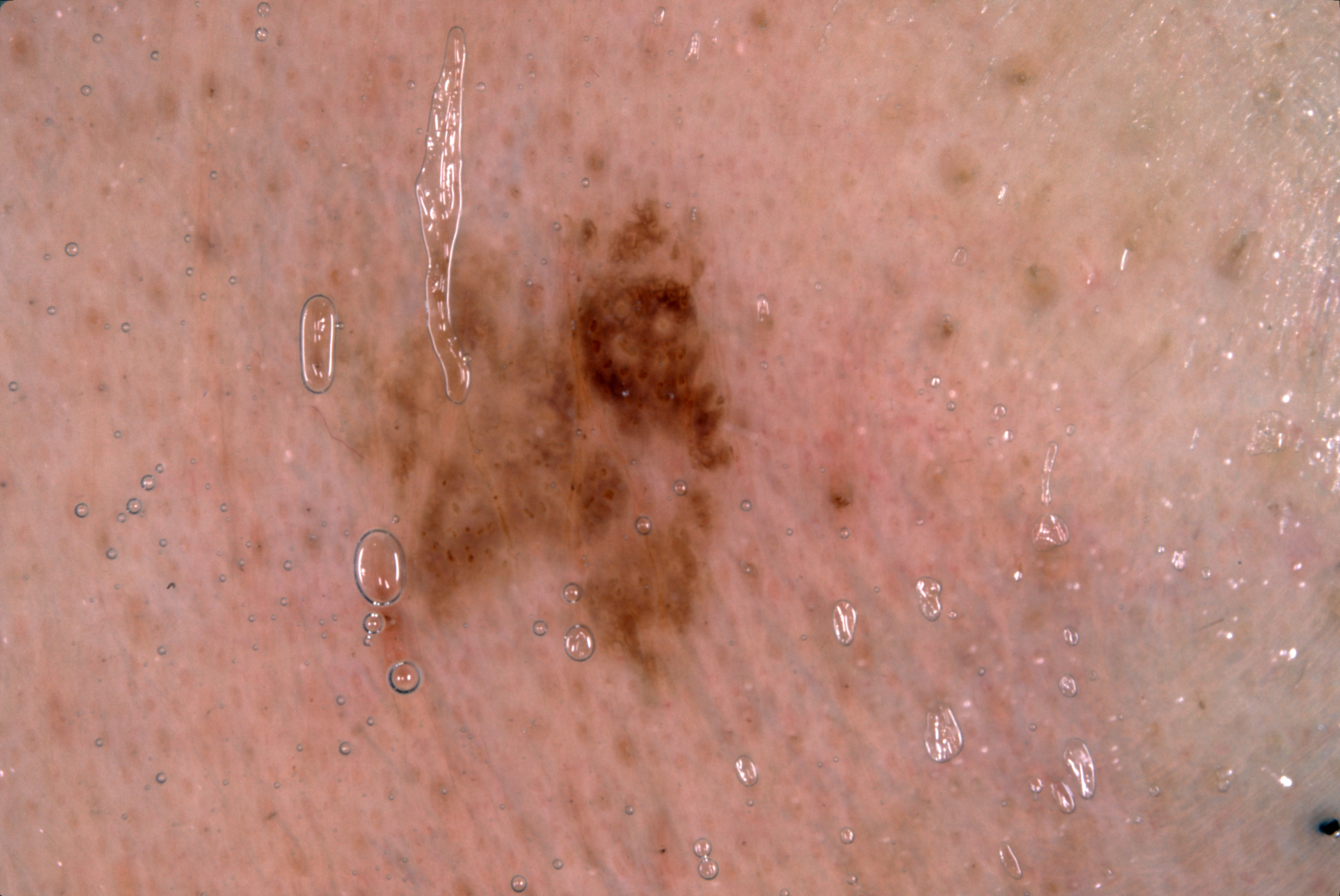A male patient aged approximately 40.
A dermoscopic close-up of a skin lesion.
The lesion spans left=356, top=210, right=743, bottom=651.
Dermoscopic examination shows pigment network and milia-like cysts; no streaks or negative network.
The lesion occupies roughly 10% of the field.
The diagnostic assessment was a seborrheic keratosis.